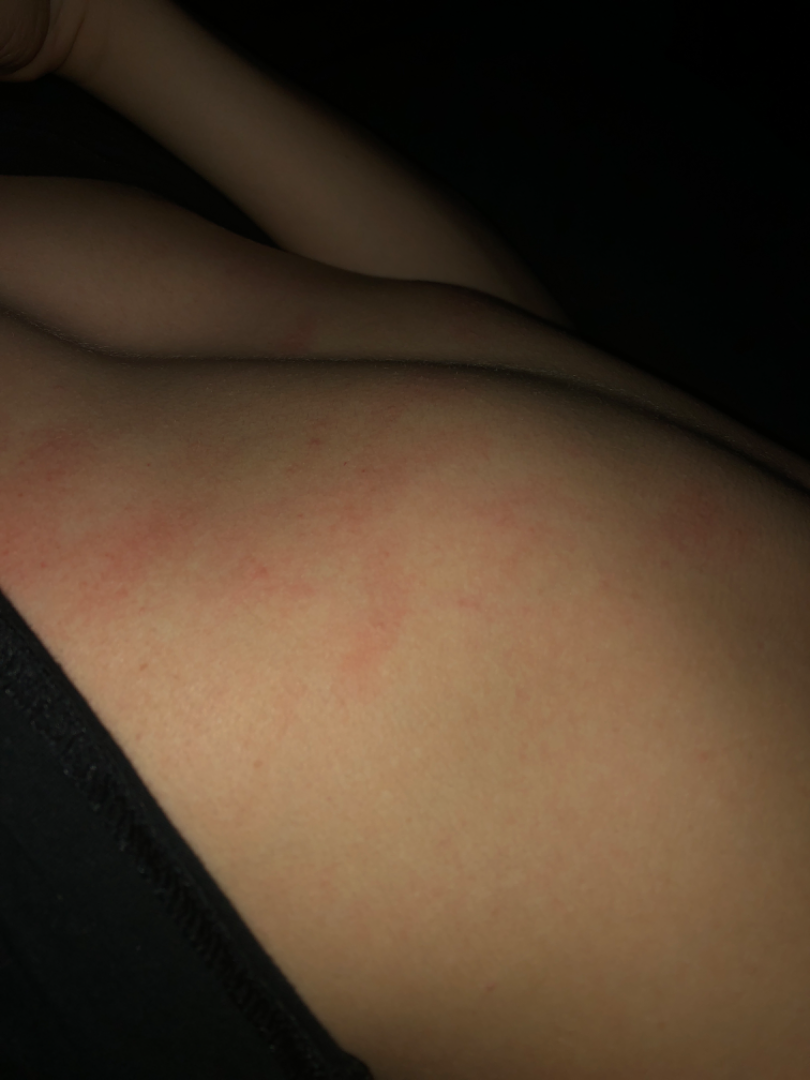Background: Self-categorized by the patient as a rash. The affected area is the front of the torso. Symptoms reported: itching. The photo was captured at an angle. Texture is reported as raised or bumpy. Male subject, age 18–29. The contributor notes the condition has been present for about one day. Findings: A single dermatologist reviewed the case: Urticaria and Eczema were each considered, in no particular order.